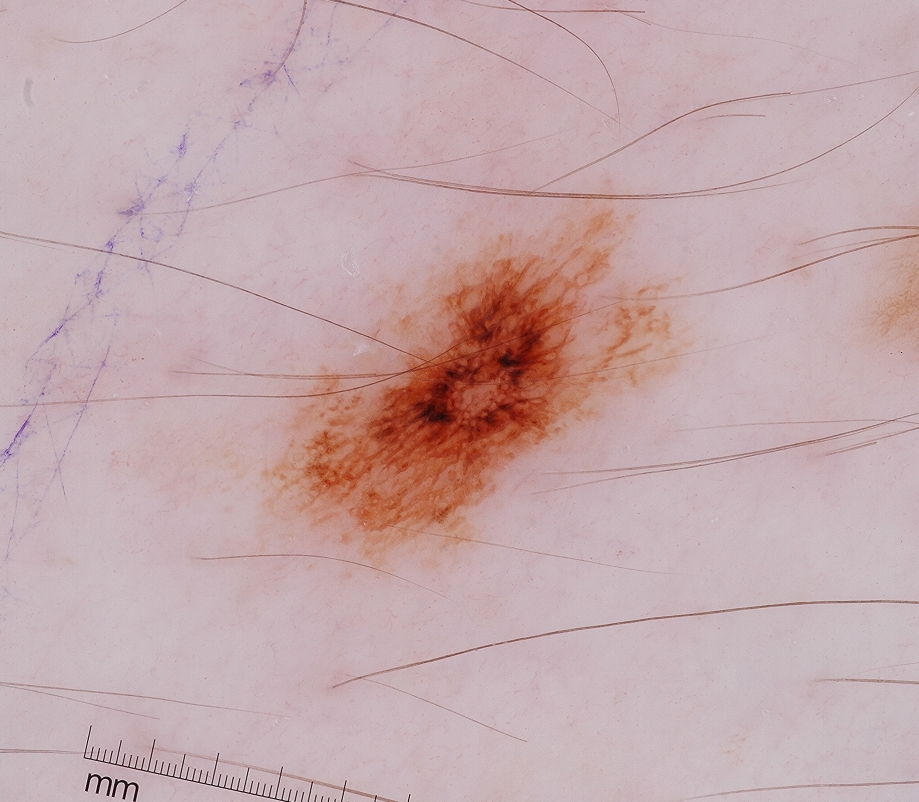image type — dermoscopy of a skin lesion | dermoscopic pattern — pigment network; absent: milia-like cysts, globules, negative network, and streaks | size — ~13% of the field | lesion bbox — 242/173/704/579 | diagnosis — a melanocytic nevus.